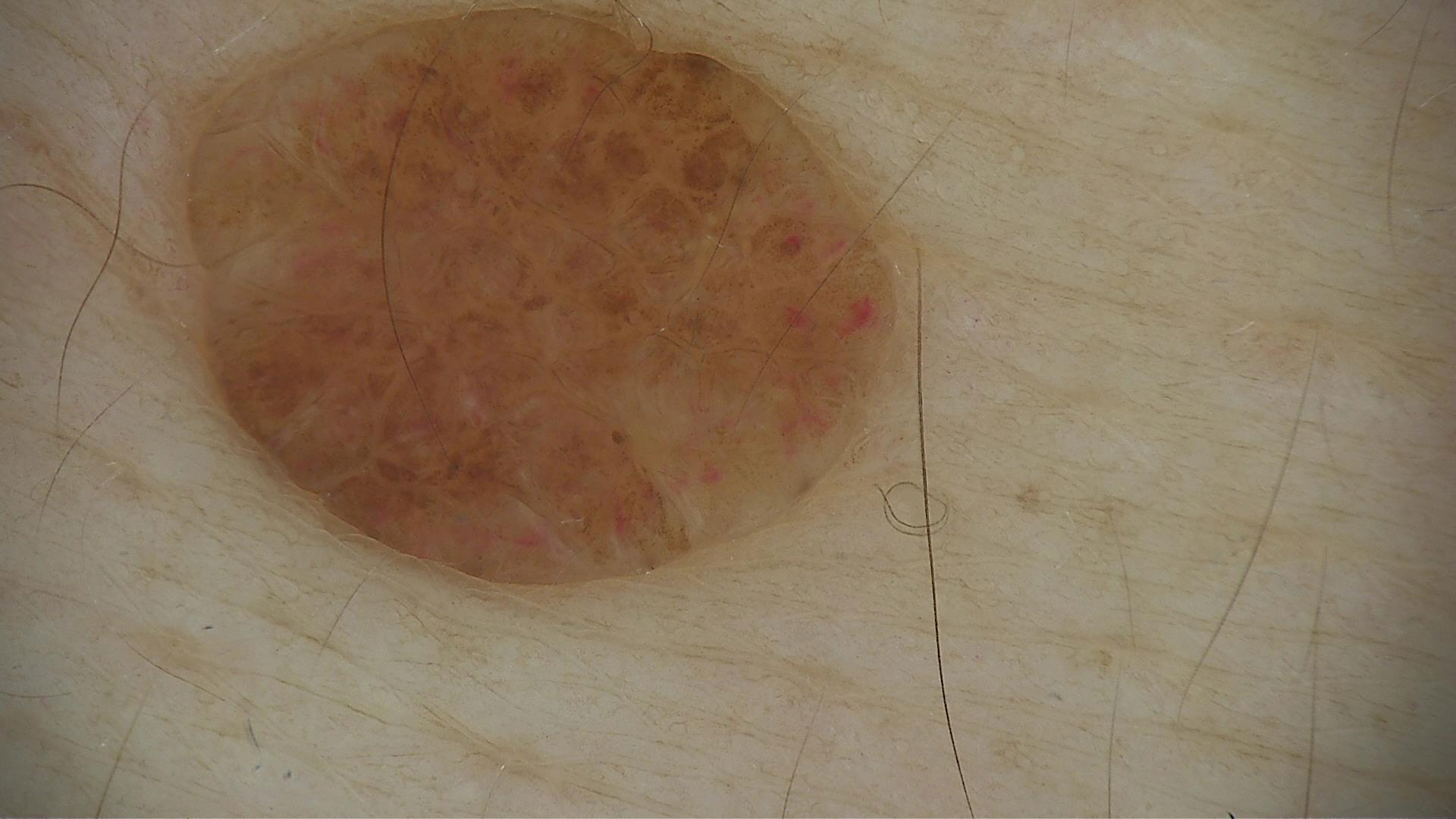image type: dermoscopy | classification: banal | assessment: dermal nevus (expert consensus).